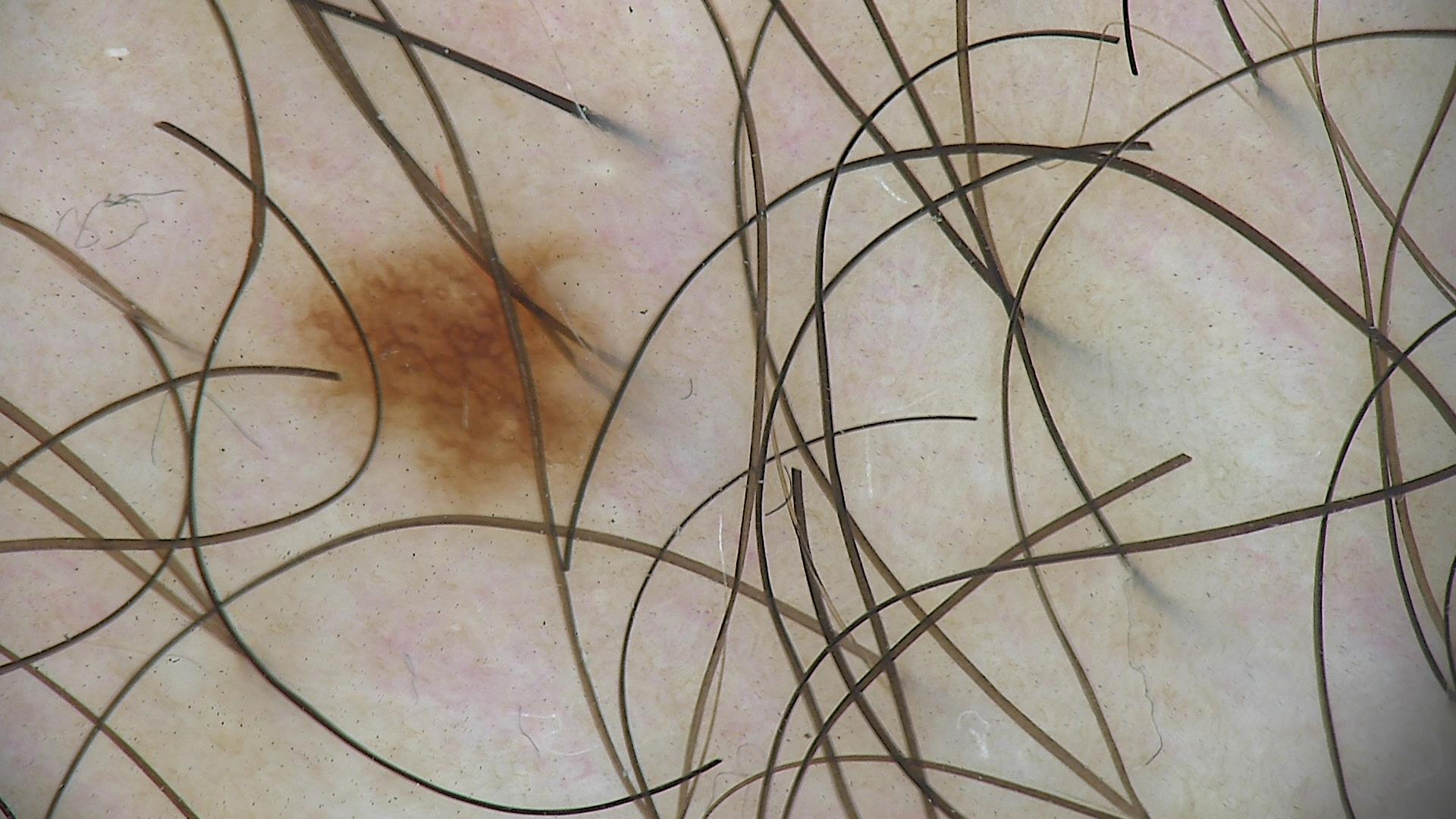{
  "image": "dermatoscopy",
  "diagnosis": {
    "name": "dysplastic junctional nevus",
    "code": "jd",
    "malignancy": "benign",
    "super_class": "melanocytic",
    "confirmation": "expert consensus"
  }
}